A skin lesion imaged with contact-polarized dermoscopy · a male subject in their 70s · the patient is FST II.
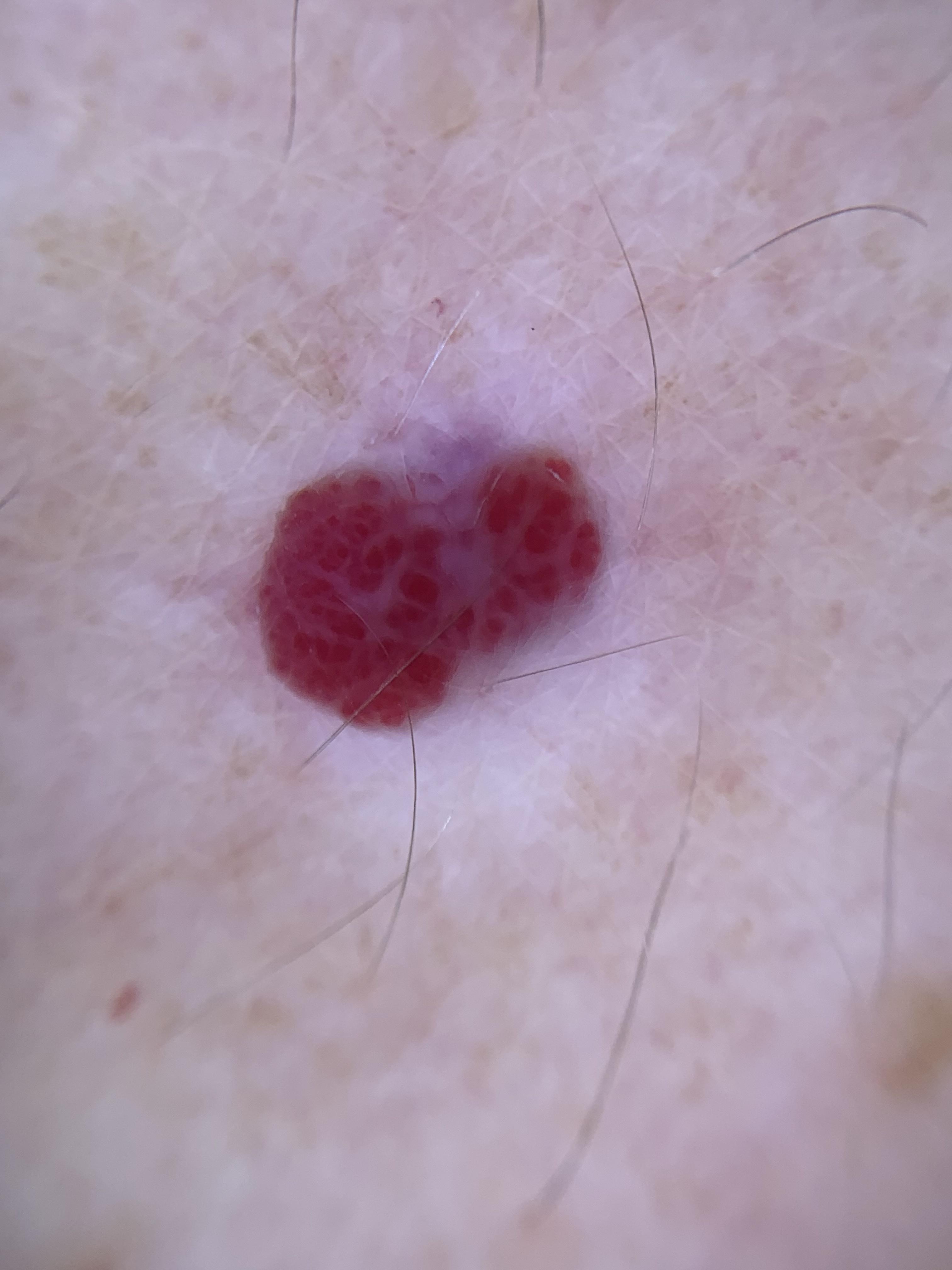Clinical context:
The lesion was found on the anterior trunk.
Impression:
Clinically diagnosed as a vascular lesion.